A female subject aged 28 to 32.
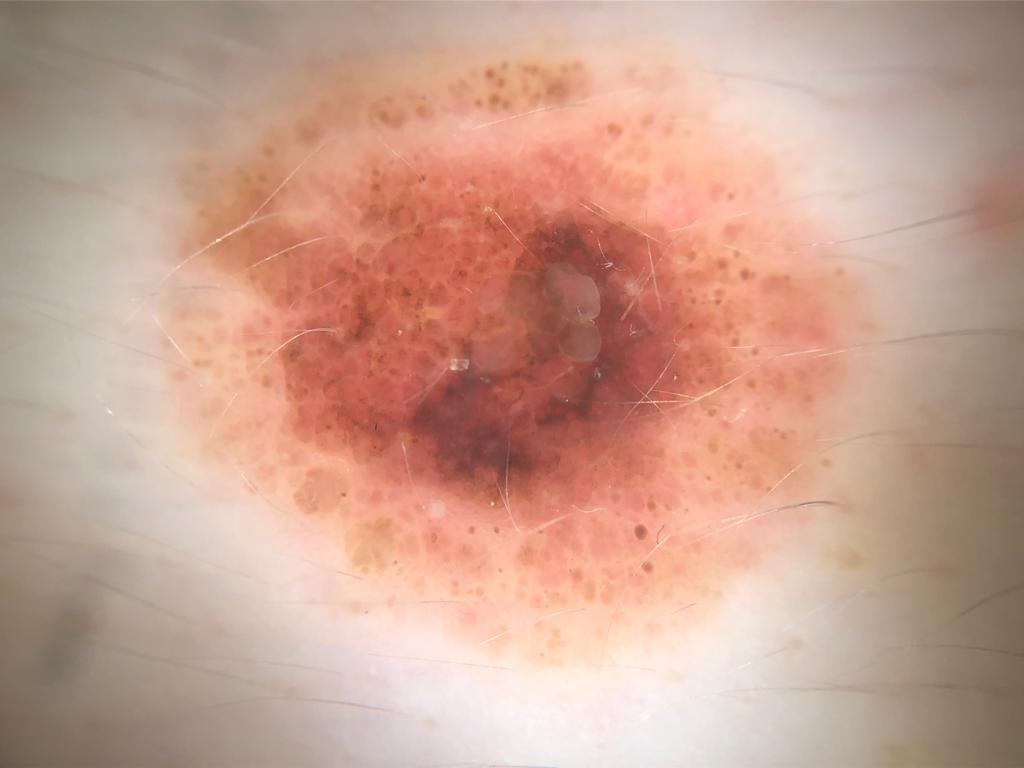site = the anterior trunk
diagnosis = Nevus (biopsy-proven)